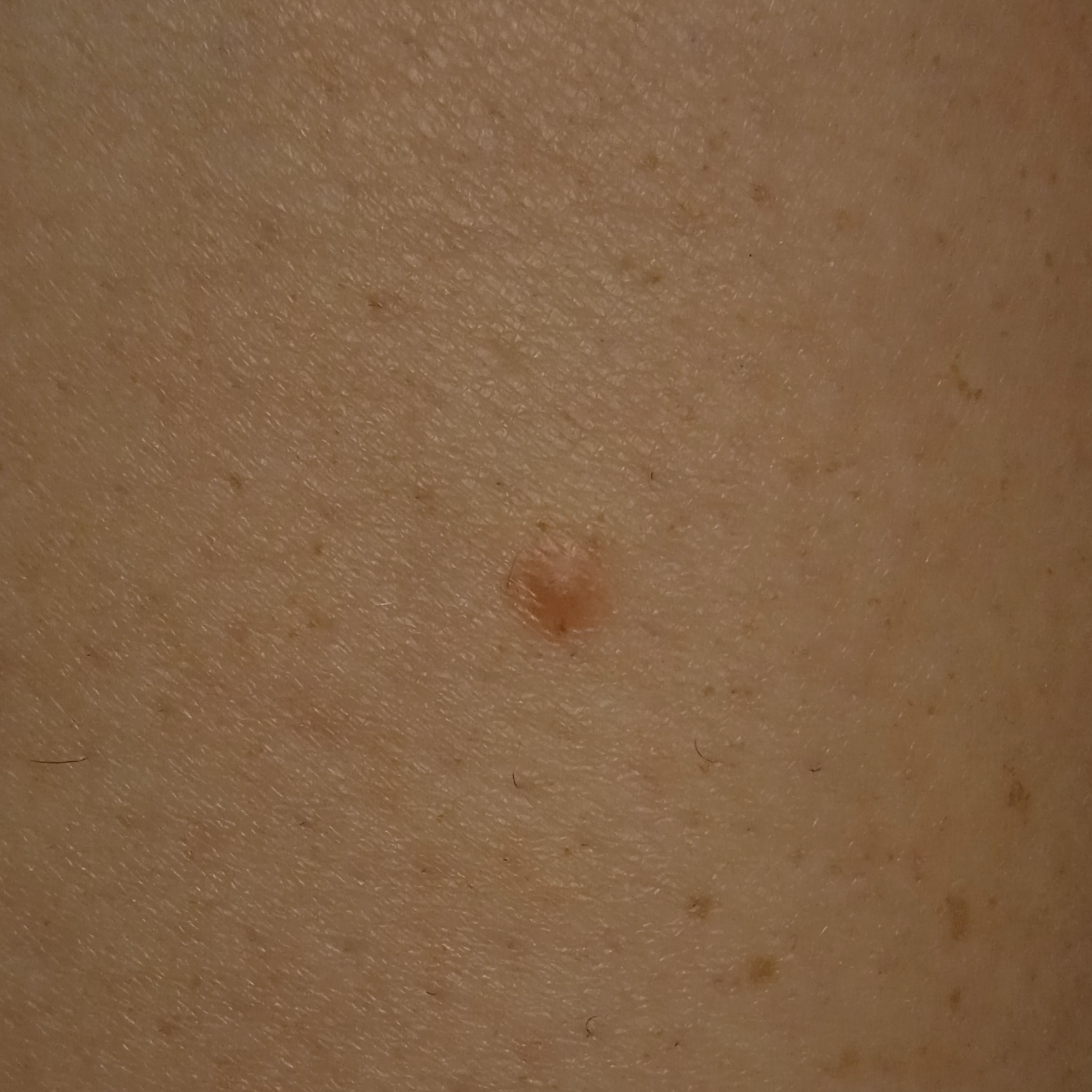{"sun_reaction": "skin reddens with sun exposure", "mole_burden": "a moderate number of melanocytic nevi", "image": "clinical photo", "referral": "research study (no referral diagnosis)", "risk_factors": {"positive": ["a personal history of skin cancer", "a personal history of cancer"], "negative": ["no sunbed use", "no prior organ transplant"]}, "patient": {"age": 32, "sex": "female"}, "diagnosis": {"name": "dermatofibroma", "malignancy": "benign"}}